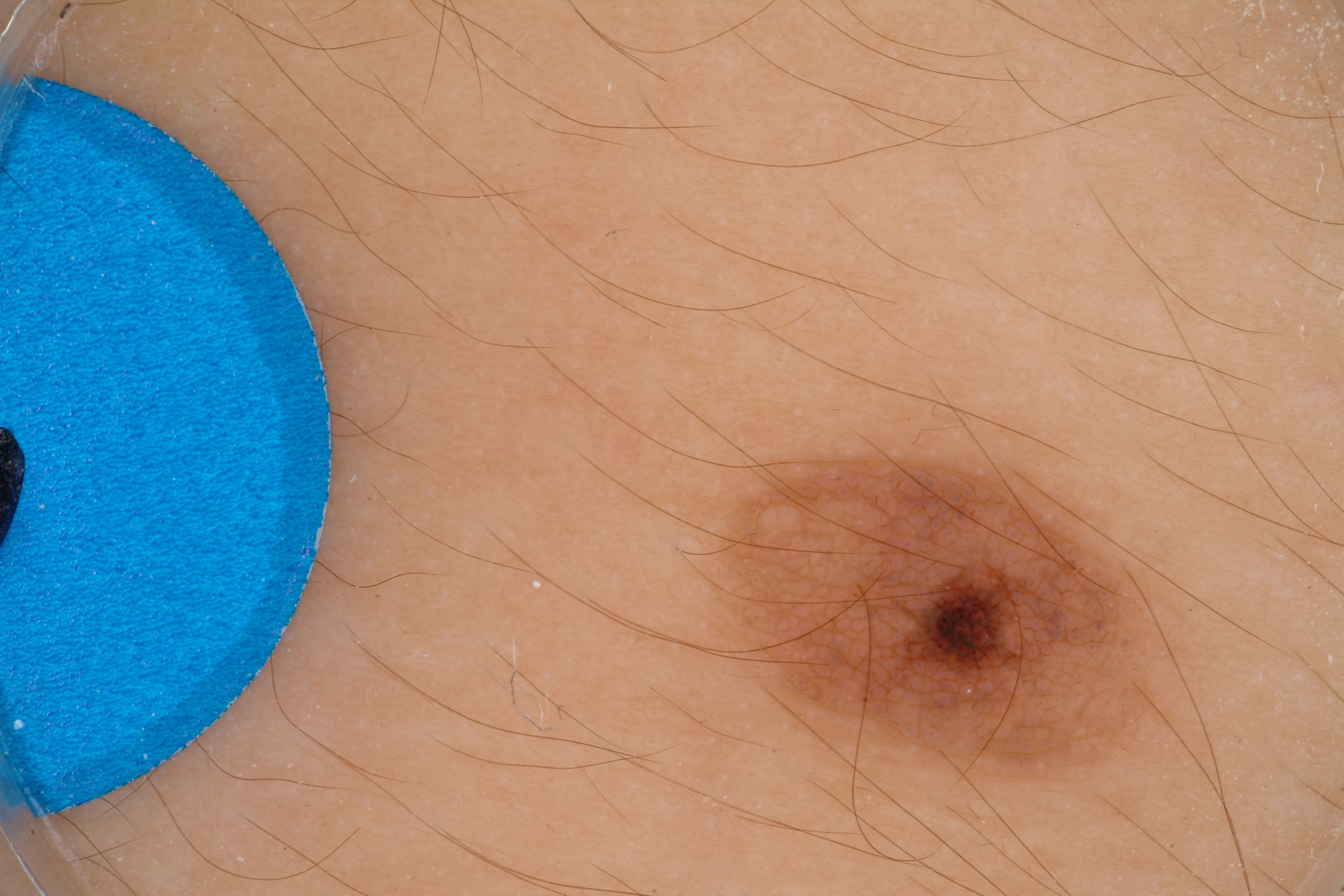A male subject, approximately 15 years of age.
A dermoscopic close-up of a skin lesion.
The lesion is located at x1=679, y1=438, x2=1169, y2=791.
Dermoscopy demonstrates globules and milia-like cysts; no pigment network, streaks, or negative network.
Clinically diagnosed as a melanocytic nevus.